The patient considered this a rash · reported lesion symptoms include pain, enlargement and itching · Fitzpatrick skin type II; human graders estimated 3 on the MST · the lesion involves the arm · the photograph is a close-up of the affected area · the lesion is described as raised or bumpy · the condition has been present for about one day:
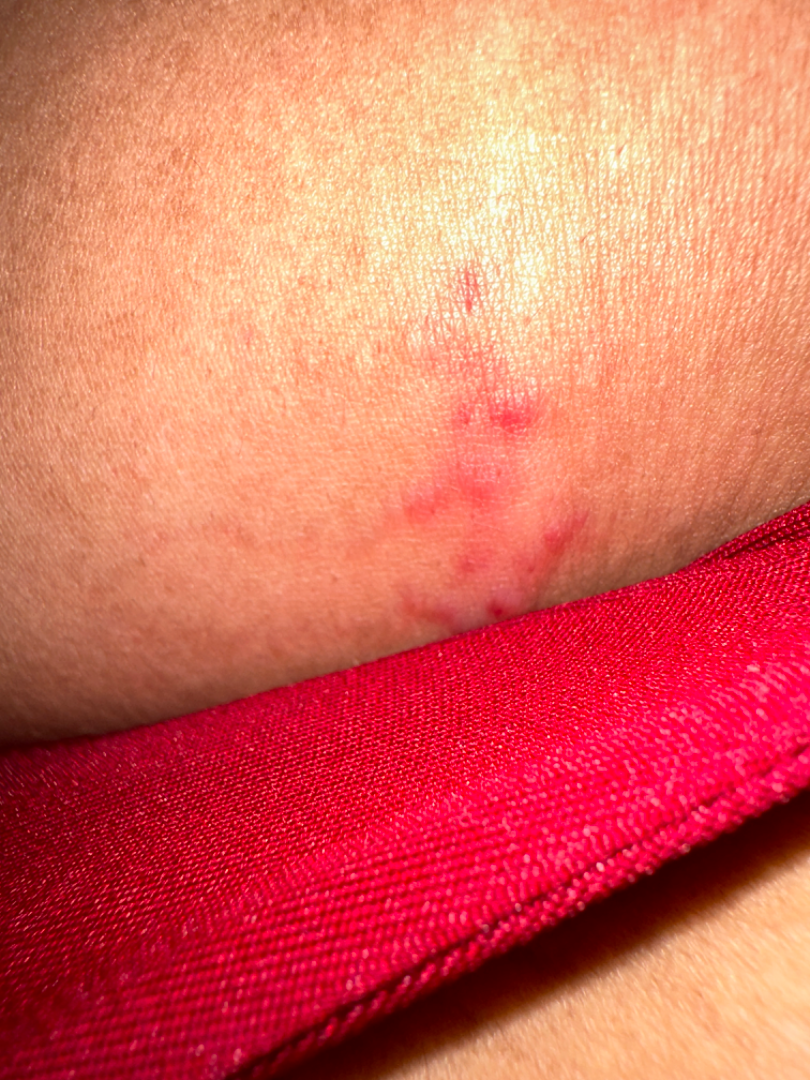Q: What is the differential diagnosis?
A: Insect Bite and Herpes Simplex were considered with similar weight